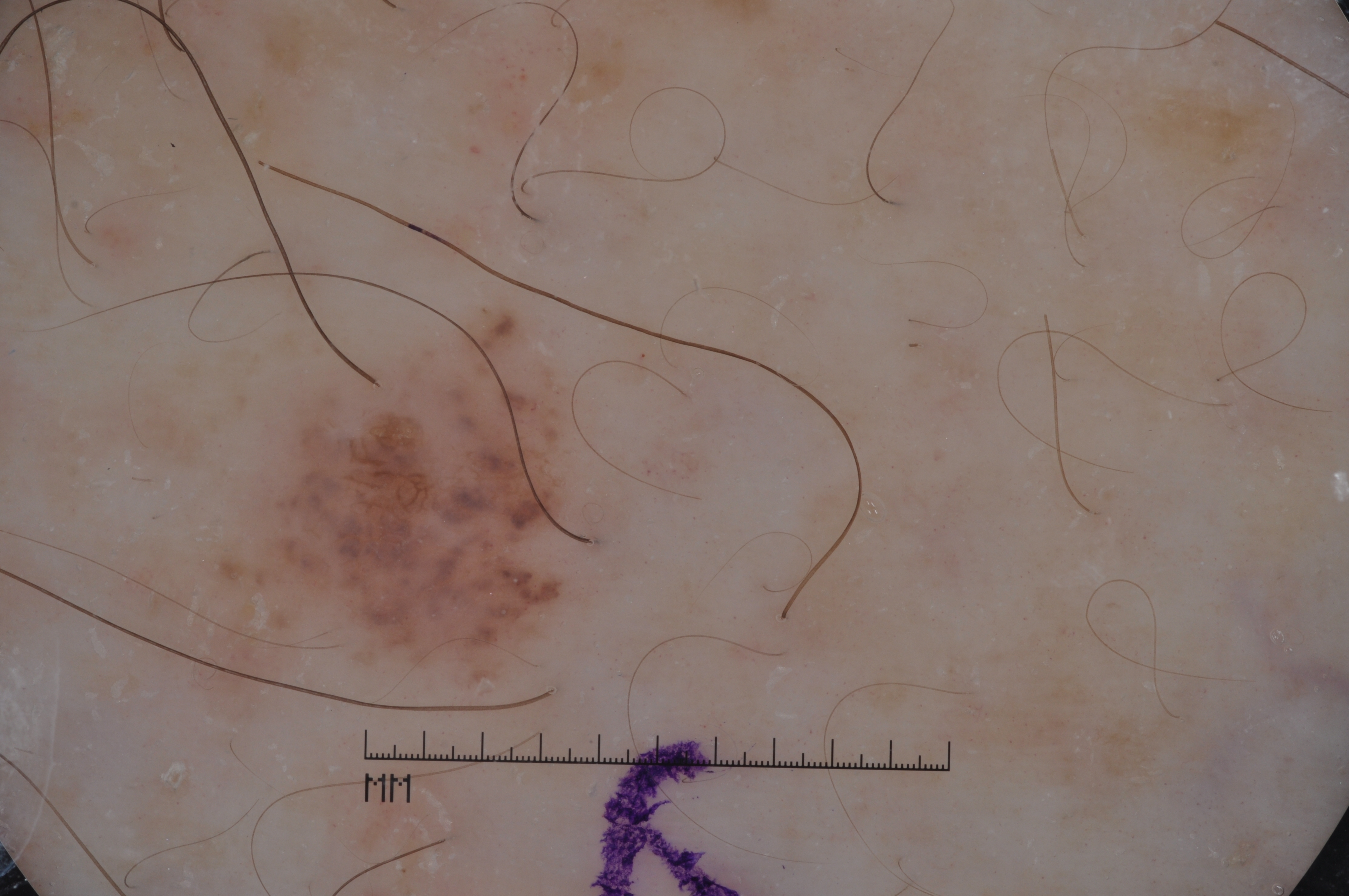Case summary: A female patient, aged around 65. A dermoscopy image of a single skin lesion. With coordinates (x1, y1, x2, y2), the lesion is bounded by 215 293 589 698. The lesion takes up about 9% of the image. Dermoscopic examination shows milia-like cysts and pigment network, with no streaks or negative network. Assessment: The clinical diagnosis was a melanocytic nevus.